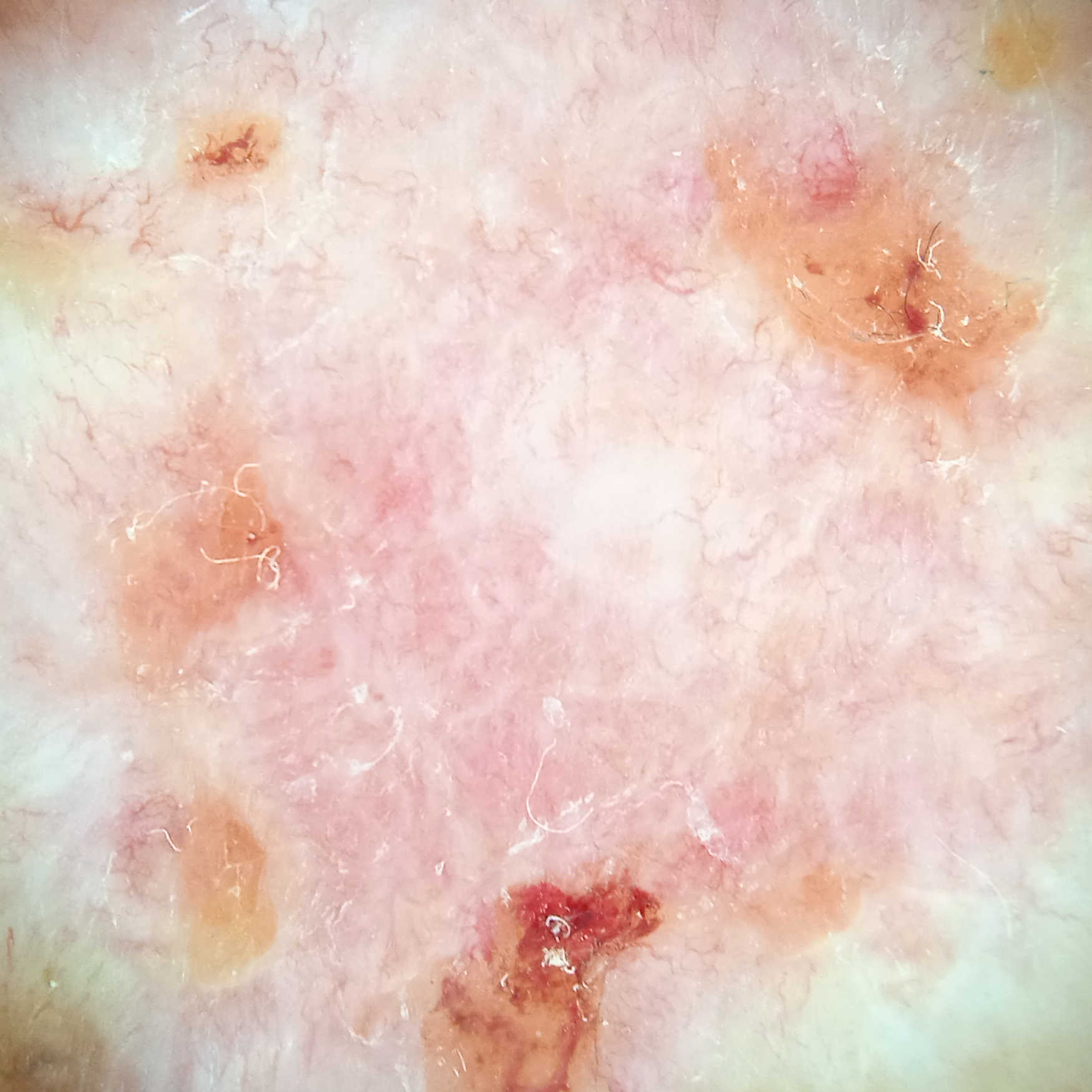A male subject aged 81.
A dermoscopic image of a skin lesion.
The referring clinician suspected basal cell carcinoma.
The lesion is located on the back.
The lesion measures approximately 12.6 mm.
Histopathology confirmed a basal cell carcinoma, following excision, with a measured tumor thickness of 3 mm.